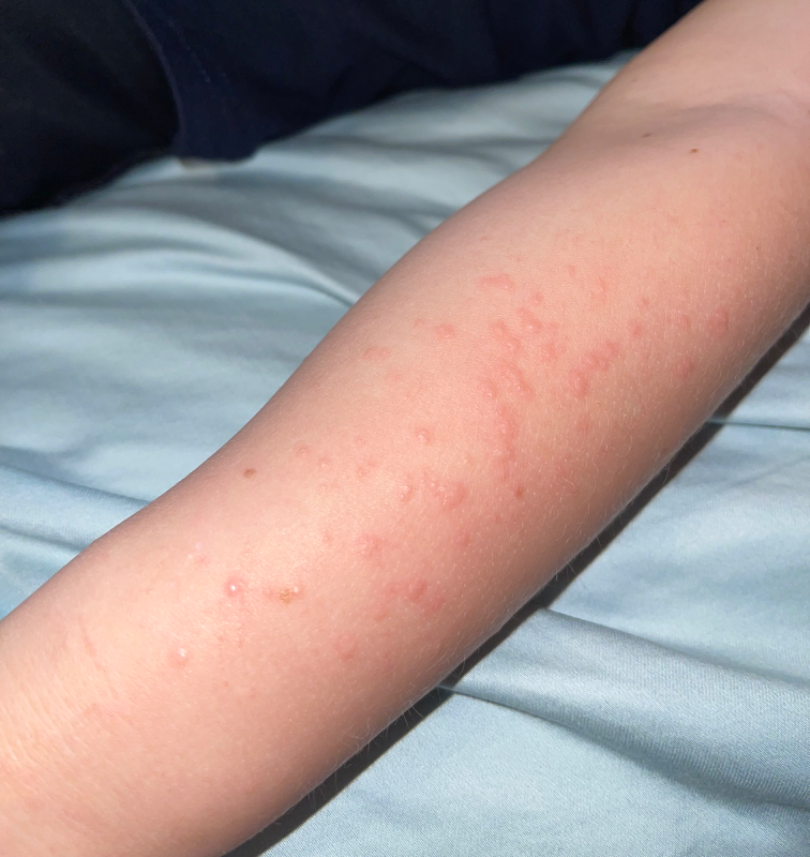On remote review of the image, most likely Urticaria; possibly Viral Exanthem.